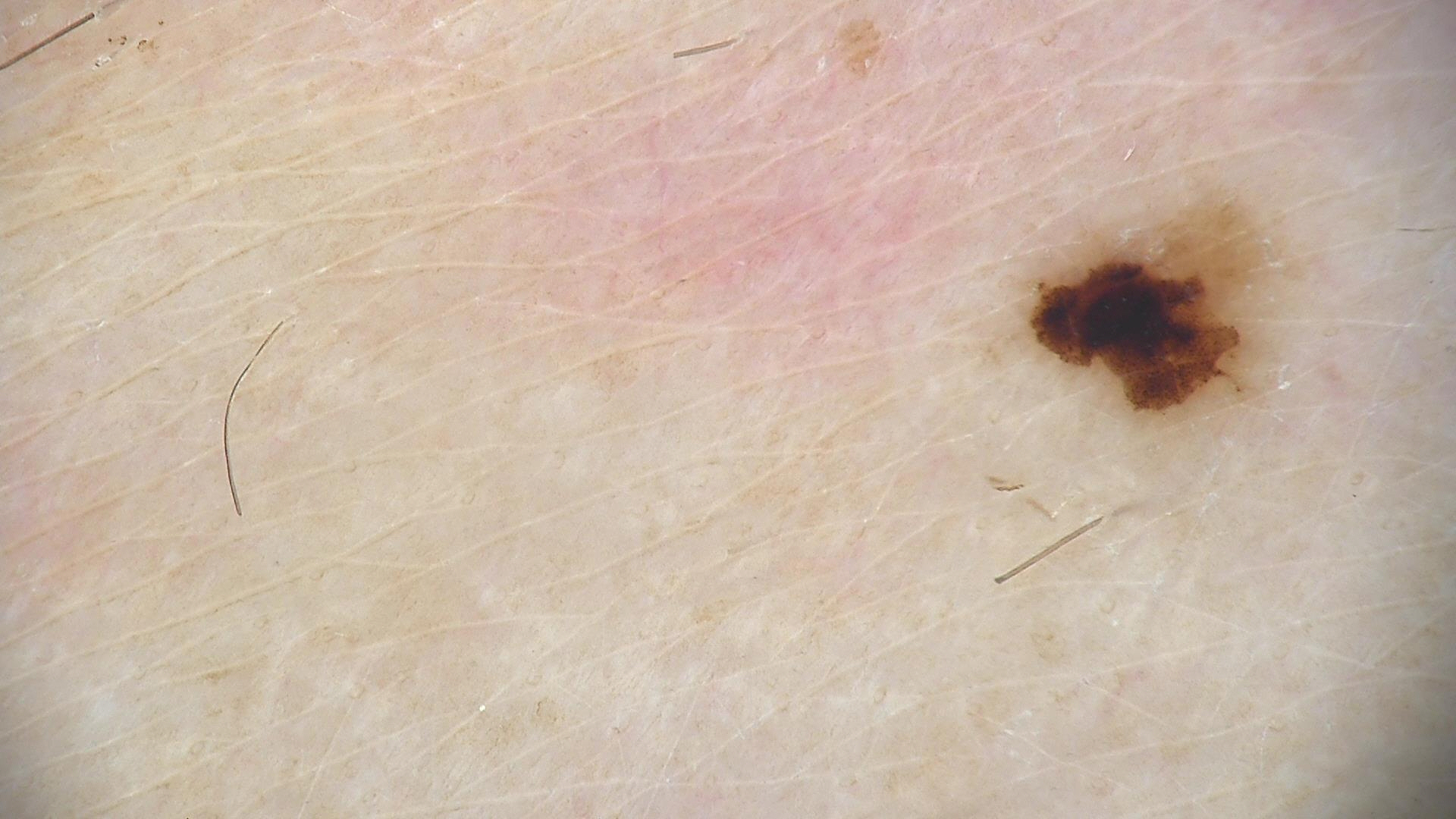label = dysplastic junctional nevus (expert consensus)